A dermoscopic close-up of a skin lesion.
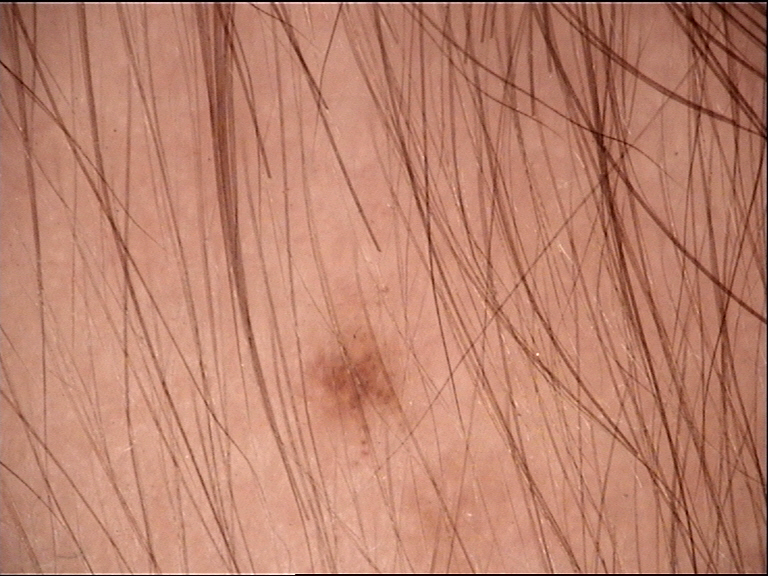{"diagnosis": {"name": "junctional nevus", "code": "jb", "malignancy": "benign", "super_class": "melanocytic", "confirmation": "expert consensus"}}